The condition has been present for one to four weeks. Associated systemic symptoms include mouth sores. This image was taken at a distance. Located on the palm. The lesion is described as rough or flaky and raised or bumpy. Symptoms reported: enlargement, pain, bothersome appearance and itching. Female contributor, age 40–49: 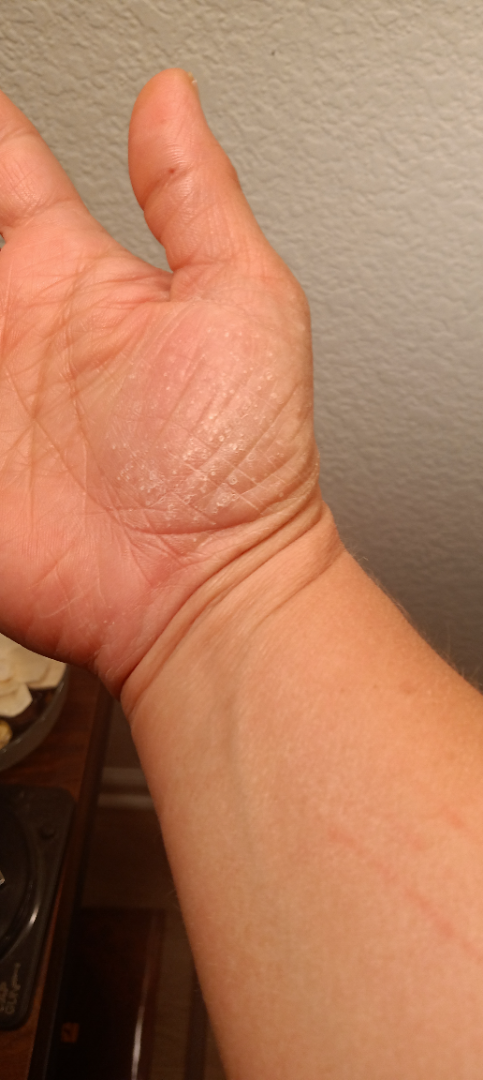On teledermatology review: Eczema (considered); Psoriasis (considered).